The lesion is described as fluid-filled, raised or bumpy and flat · the photo was captured at a distance · no relevant systemic symptoms · located on the leg · the contributor is female · the condition has been present for one to four weeks · reported lesion symptoms include itching, enlargement and bothersome appearance: 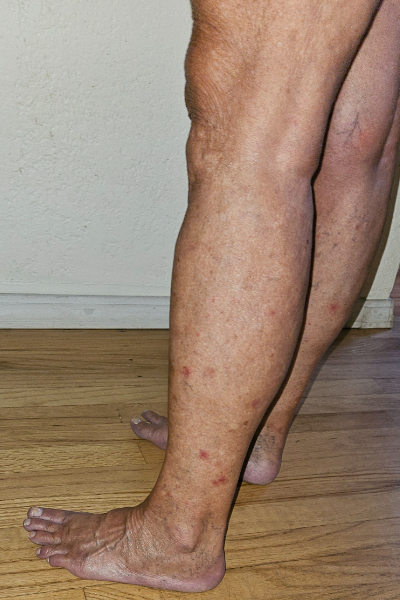Findings: Reviewed remotely by one dermatologist: the differential, in no particular order, includes Insect Bite, Eczema and Leukocytoclastic Vasculitis.